A dermoscopy image of a single skin lesion.
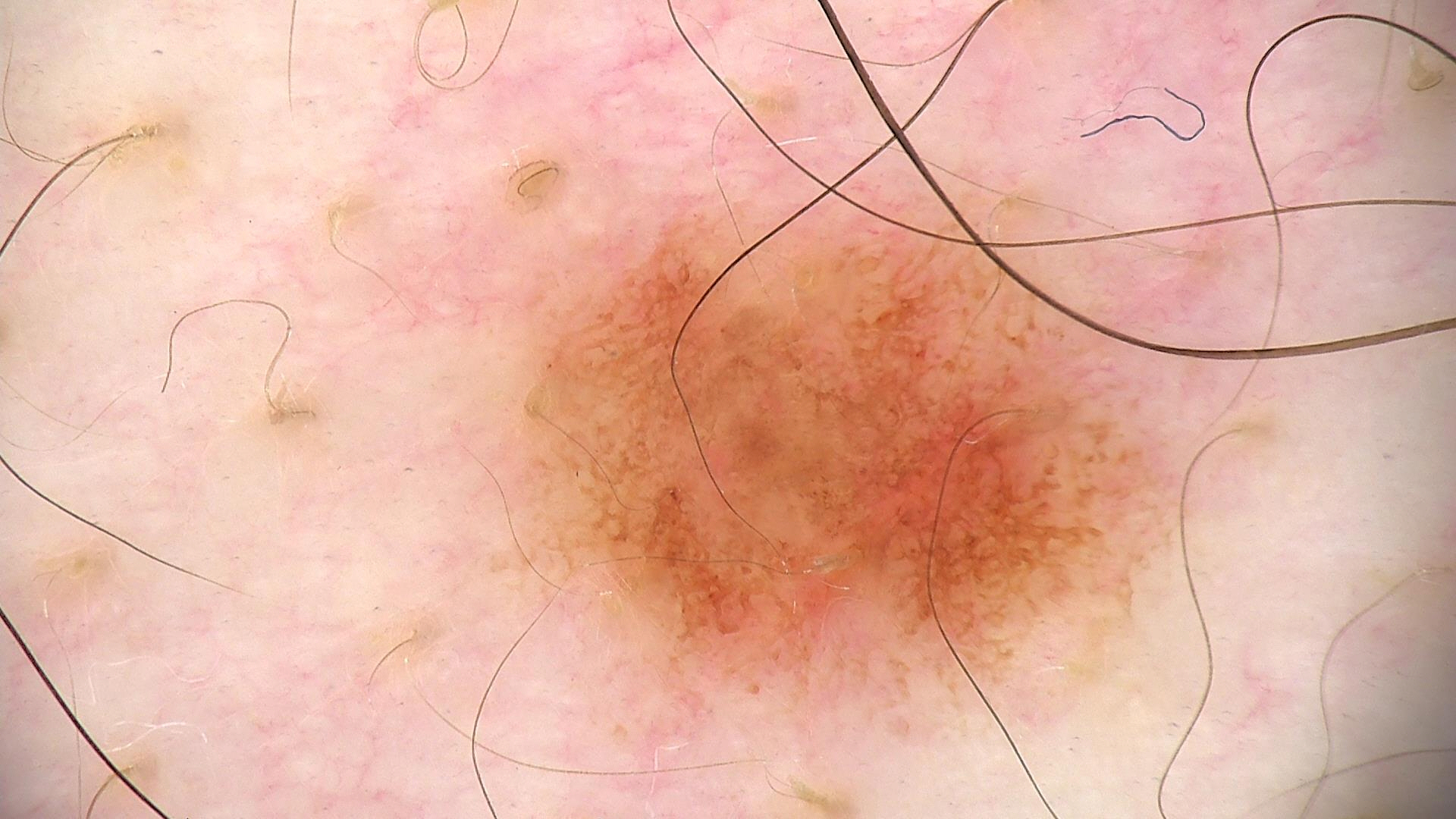Case:
– assessment — dysplastic junctional nevus (expert consensus)